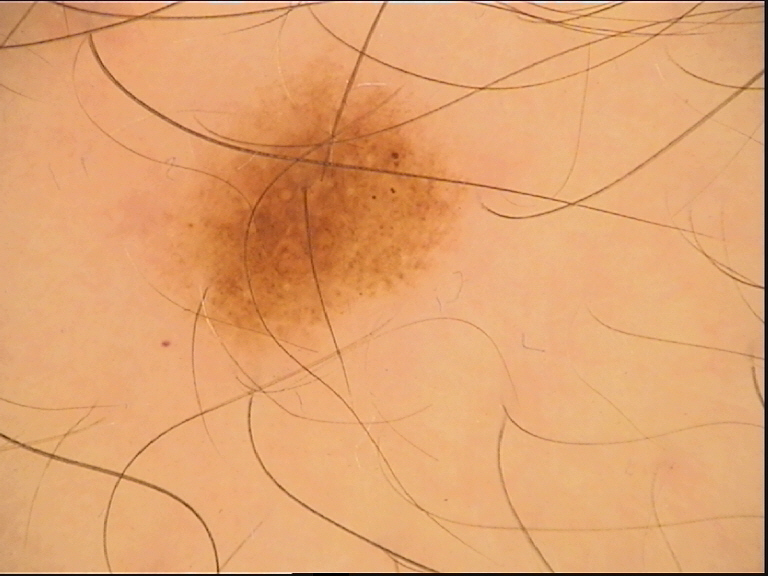A dermatoscopic image of a skin lesion.
Diagnosed as a benign lesion — a dysplastic junctional nevus.